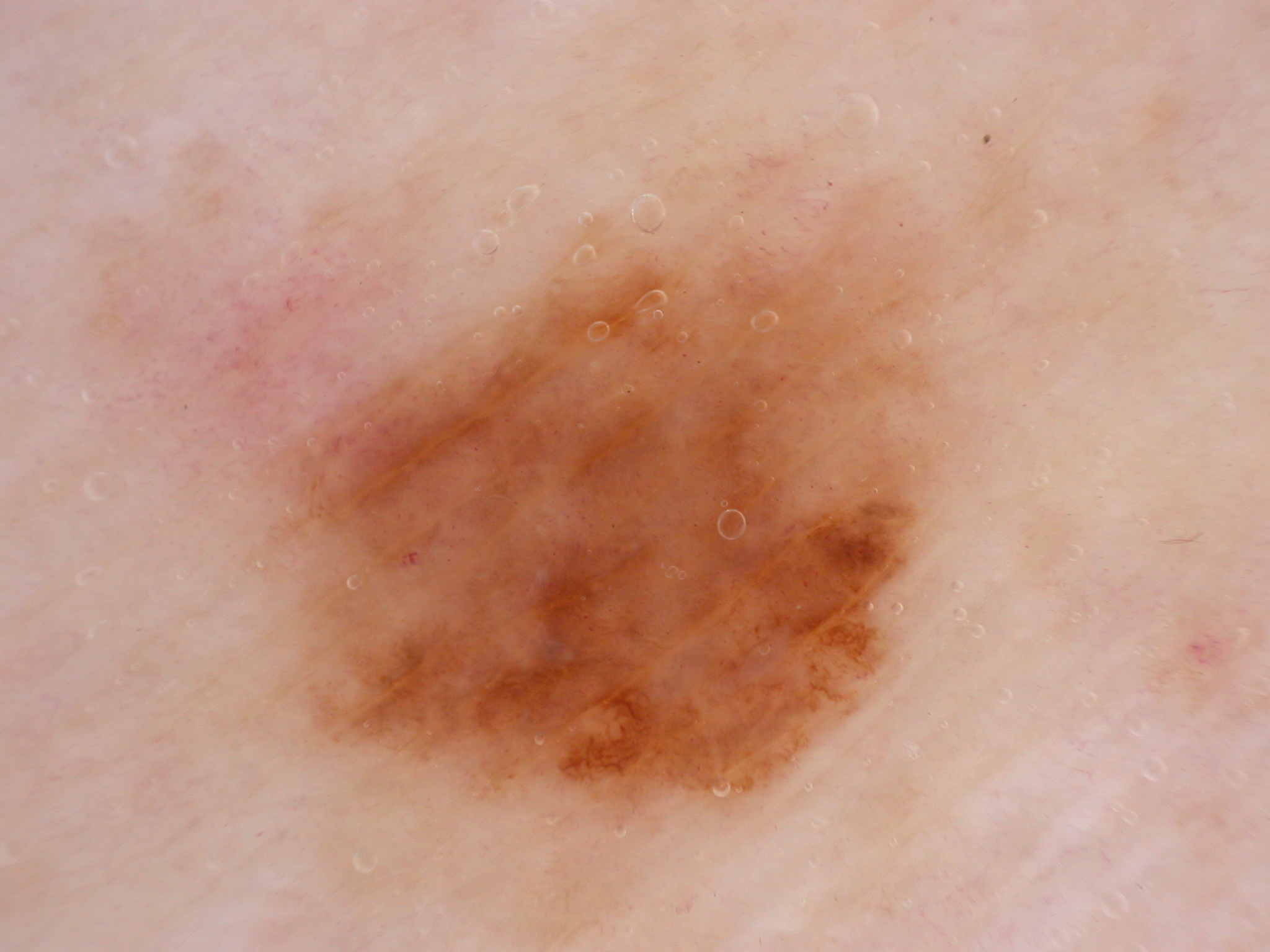A dermoscopy image of a single skin lesion.
A prominent lesion filling much of the field.
The visible lesion spans x1=81 y1=107 x2=953 y2=833.
Dermoscopically, the lesion shows pigment network; no negative network, milia-like cysts, globules, or streaks.
Diagnosed as a melanocytic nevus, a benign skin lesion.